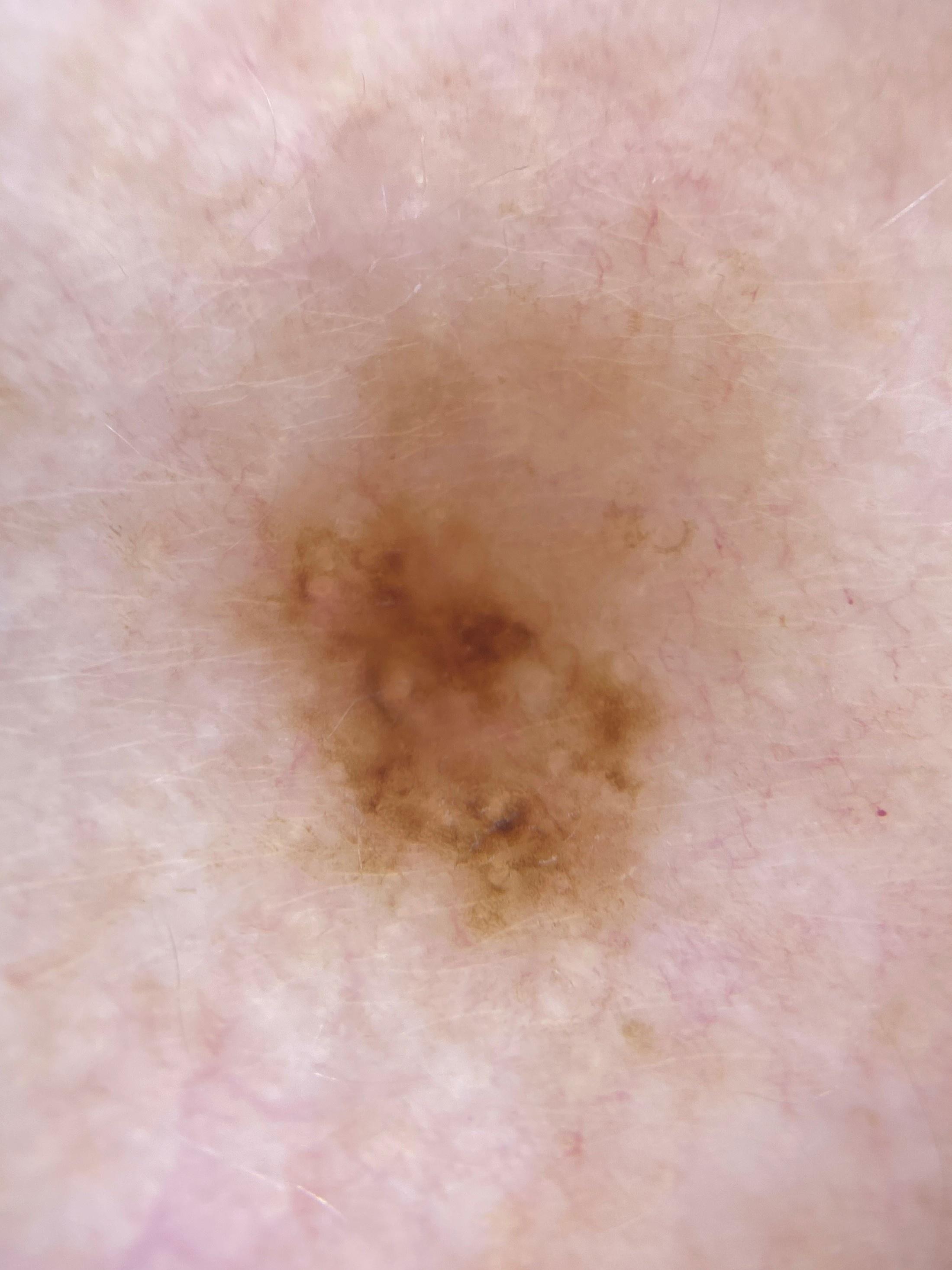relevant background = a prior melanoma
subject = female, in their mid- to late 70s
FST = II
imaging = contact-polarized dermoscopy
body site = an upper extremity
pathology = Nevus (biopsy-proven)